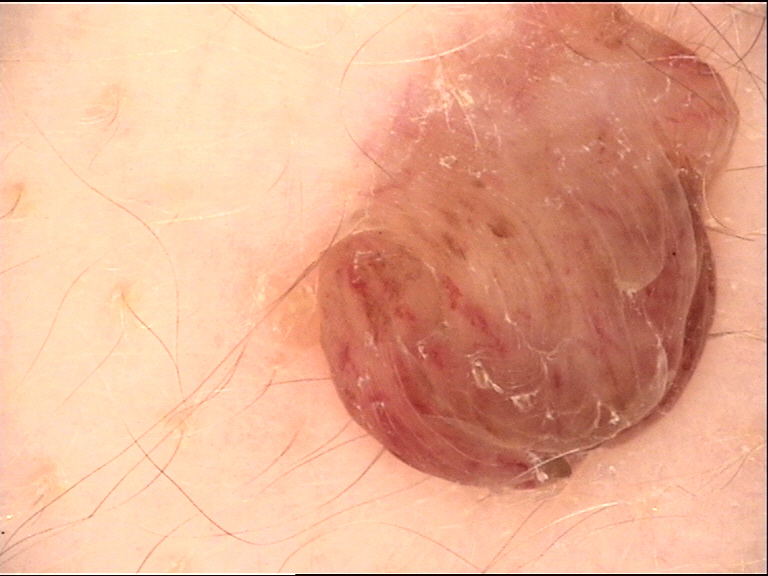Q: What kind of image is this?
A: dermoscopy
Q: What is the lesion category?
A: banal
Q: What is this lesion?
A: dermal nevus (expert consensus)